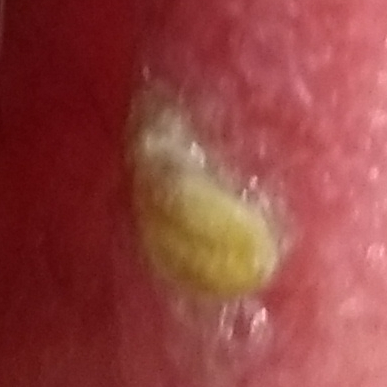A clinical photo of a skin lesion taken with a smartphone.
The chart records prior skin cancer (patient or family) and pesticide exposure.
A male subject in their mid-40s.
The lesion involves an ear.
The lesion measures approximately 5 × 4 mm.
The patient describes that the lesion is elevated, has grown, and itches.
On biopsy, the diagnosis was a squamous cell carcinoma.